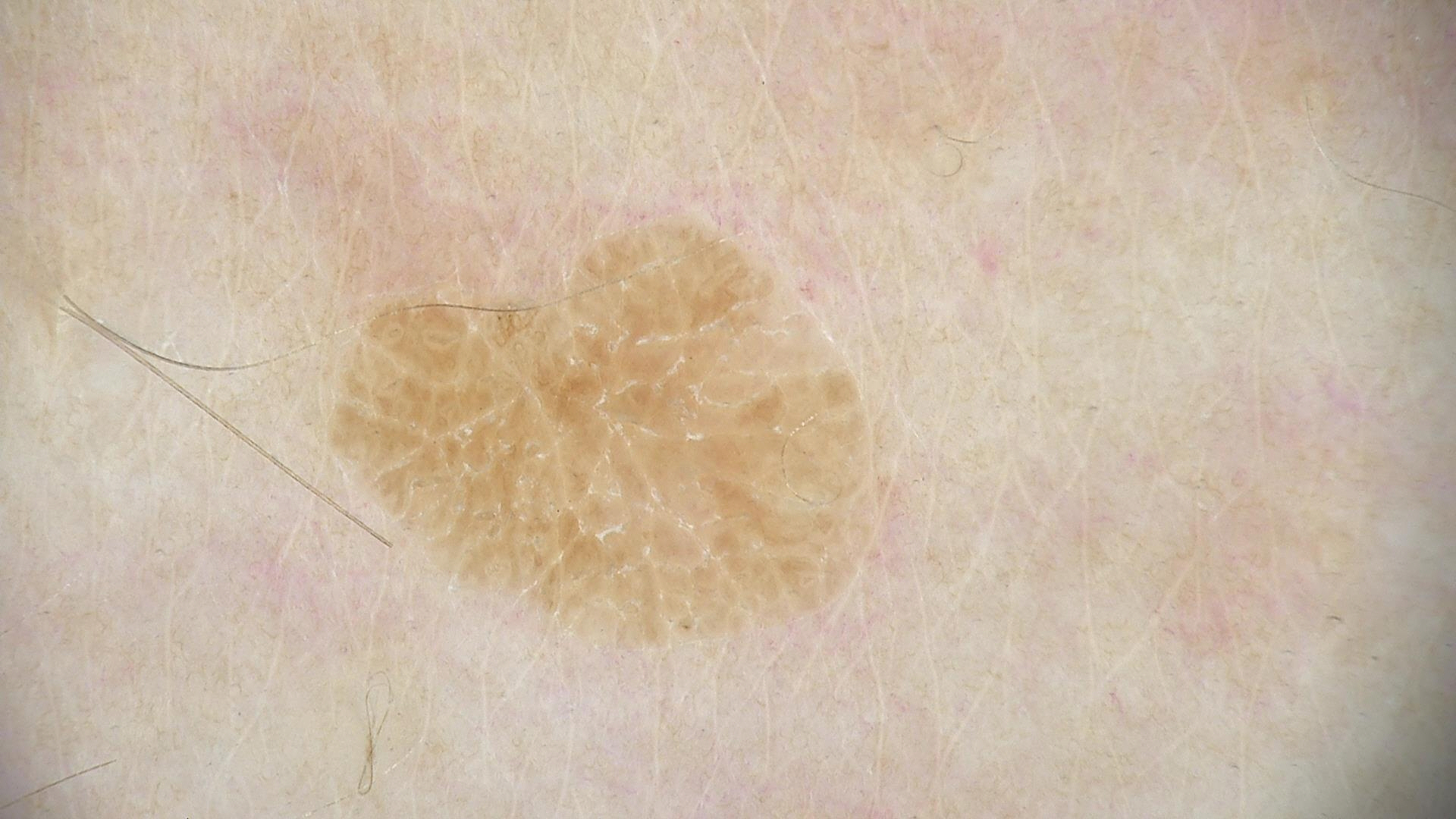Q: What is this lesion?
A: seborrheic keratosis (expert consensus)